The patient says their skin tans without first burning · a clinical photograph showing a skin lesion · a female patient 78 years old:
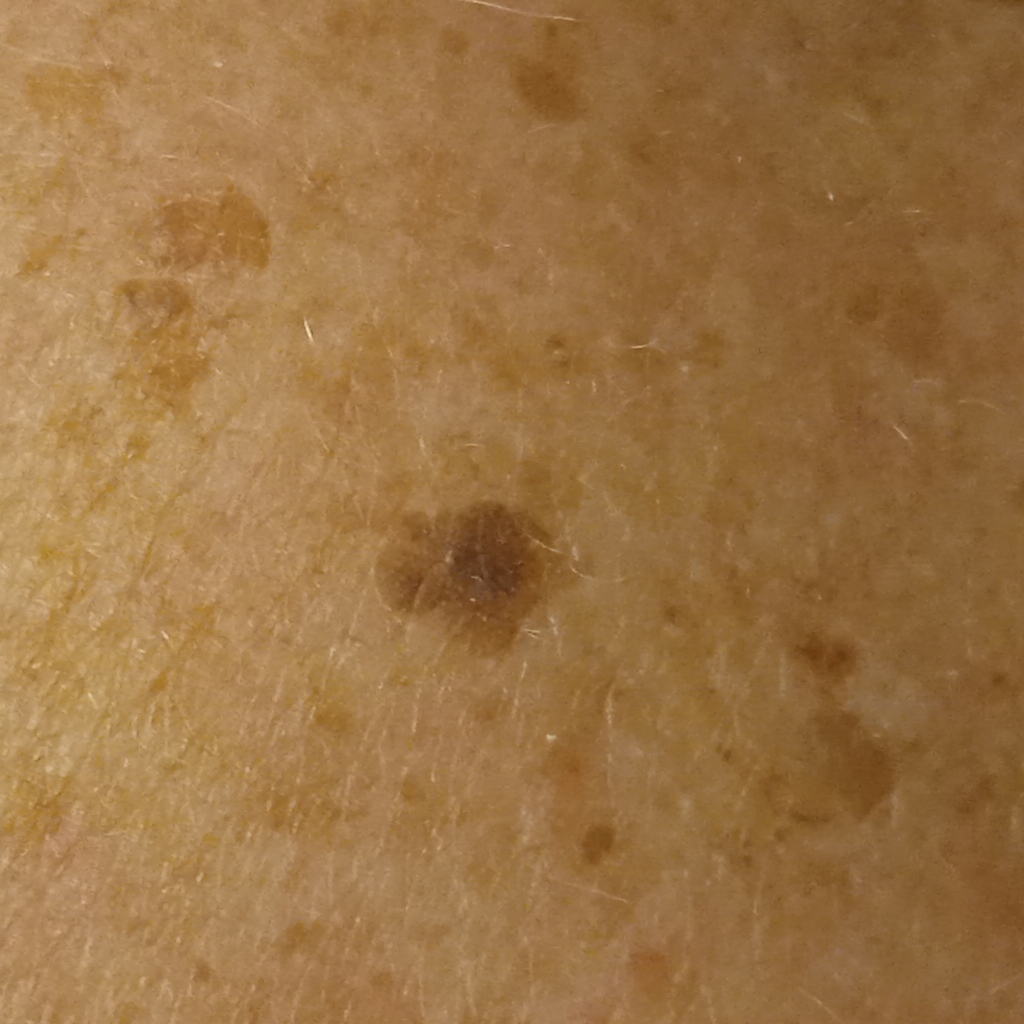body site — the back
size — 5.6 mm
diagnosis — seborrheic keratosis (dermatologist consensus)